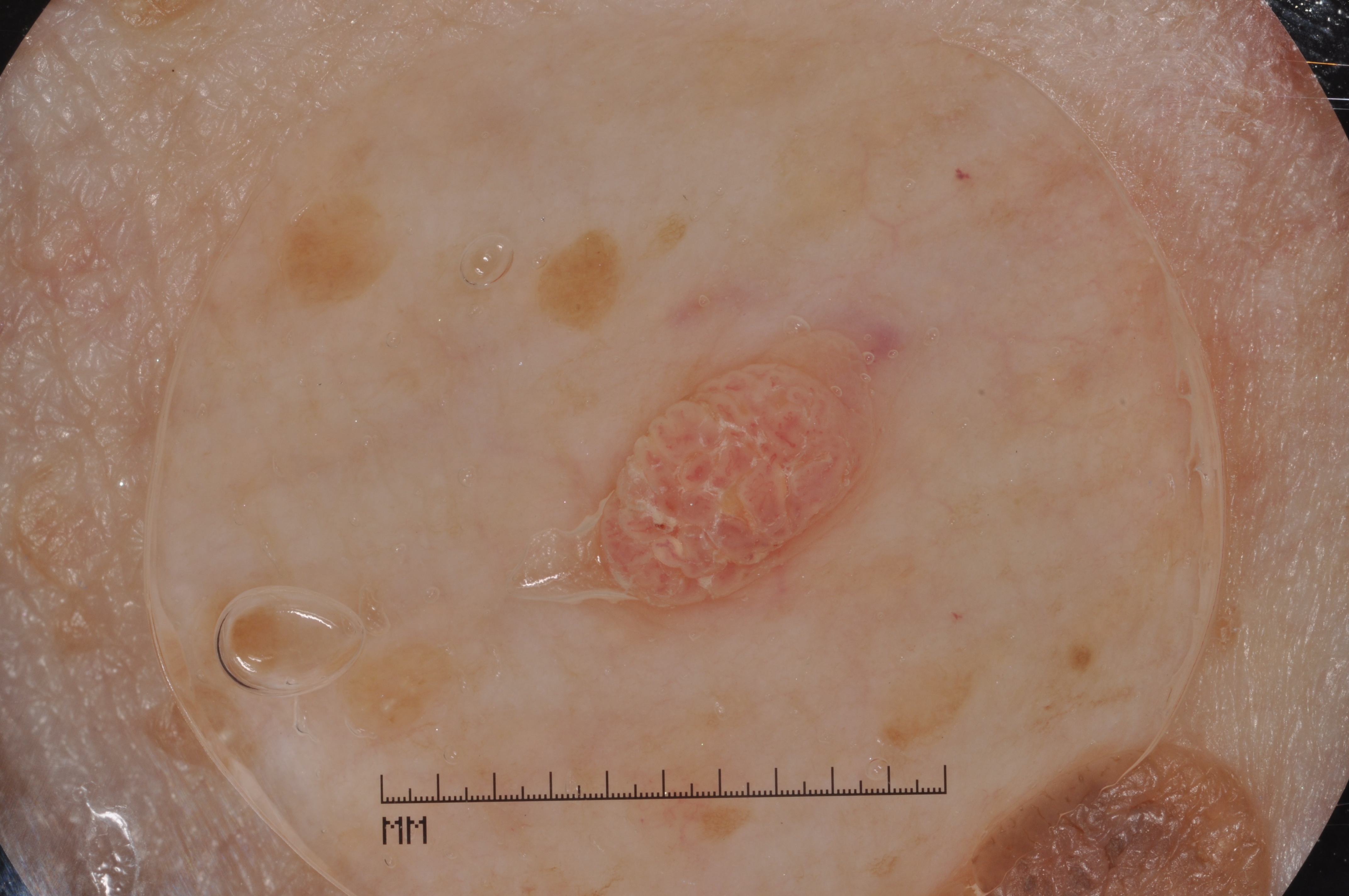The subject is a female aged around 75. A dermatoscopic image of a skin lesion. Dermoscopic examination shows no pigment network, negative network, milia-like cysts, or streaks. A small lesion occupying a minor part of the field. The visible lesion spans x1=580, y1=329, x2=896, y2=630. Diagnosed as a seborrheic keratosis.